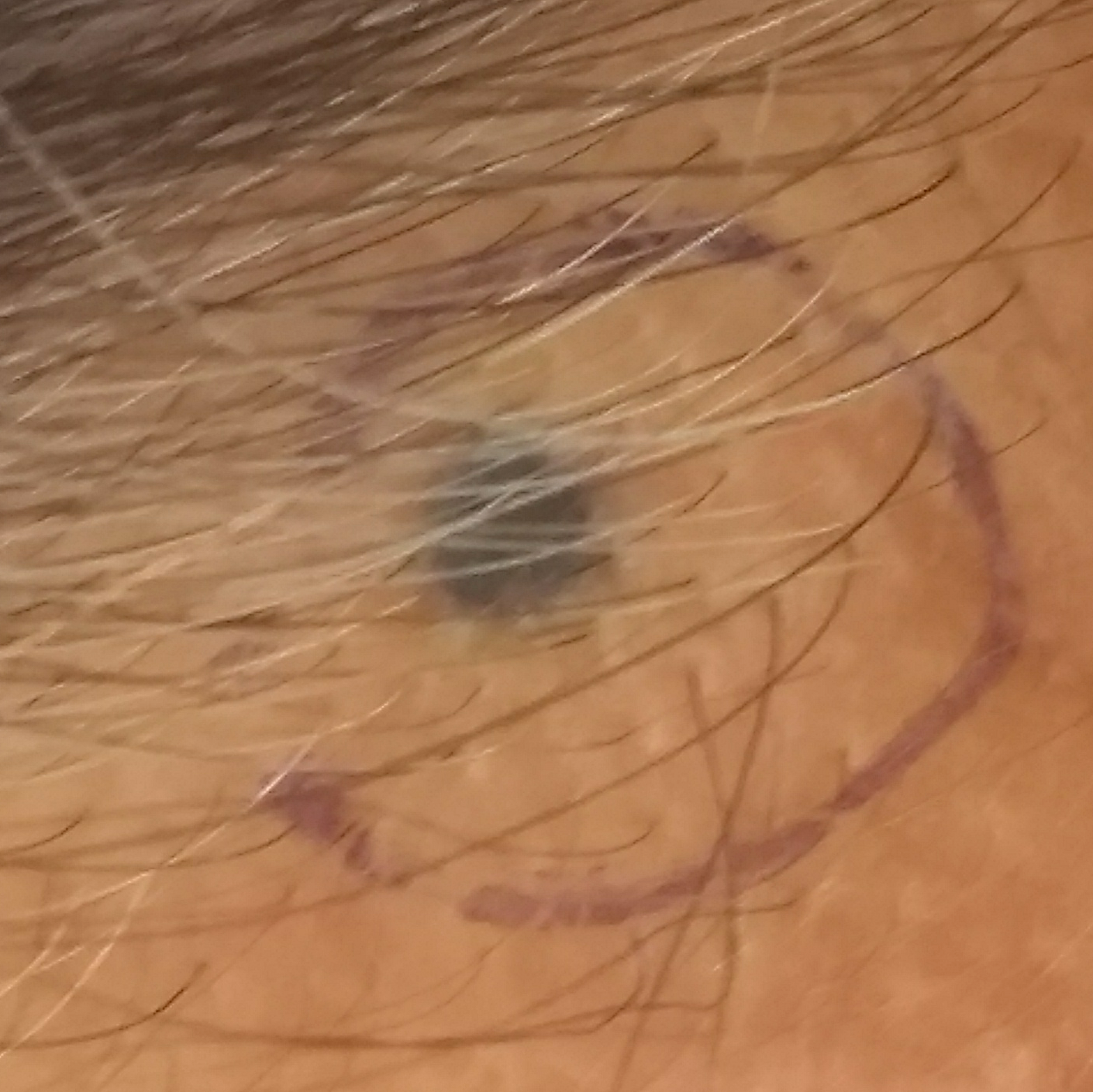A smartphone photograph of a skin lesion. A female patient in their early 80s. Located on the face. The lesion measures approximately 3 × 3 mm. Per patient report, the lesion has grown. Histopathological examination showed a nevus.